A clinical photograph showing a skin lesion. A female patient aged 73 — 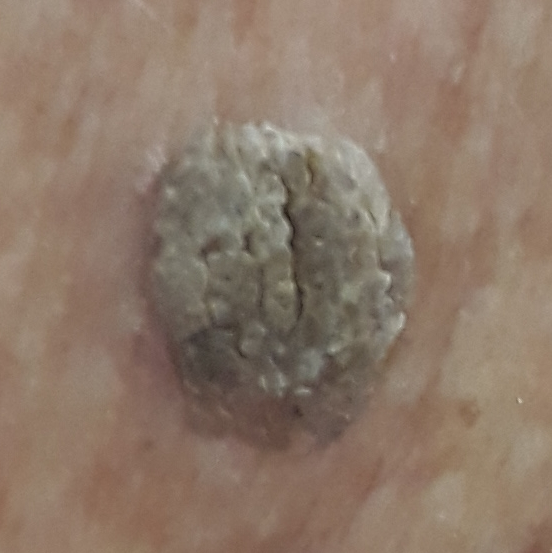The lesion is on the back.
Expert review favored a seborrheic keratosis.